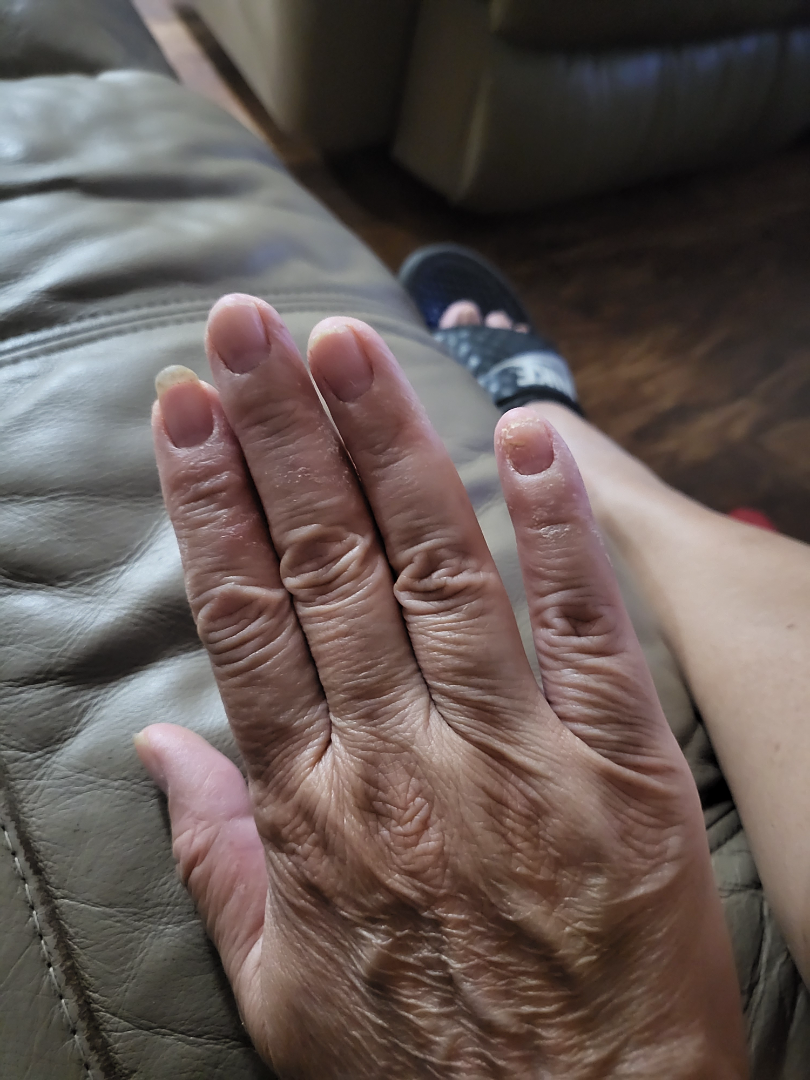Q: Could the case be diagnosed?
A: no clear pathology
Q: Anatomic location?
A: palm and back of the hand
Q: Duration?
A: three to twelve months
Q: Fitzpatrick or Monk tone?
A: human graders estimated Monk skin tone scale 2
Q: Reported symptoms?
A: none reported
Q: Texture?
A: rough or flaky
Q: How was the photo taken?
A: at a distance
Q: Patient's own categorization?
A: a nail problem